A dermoscopy image of a single skin lesion.
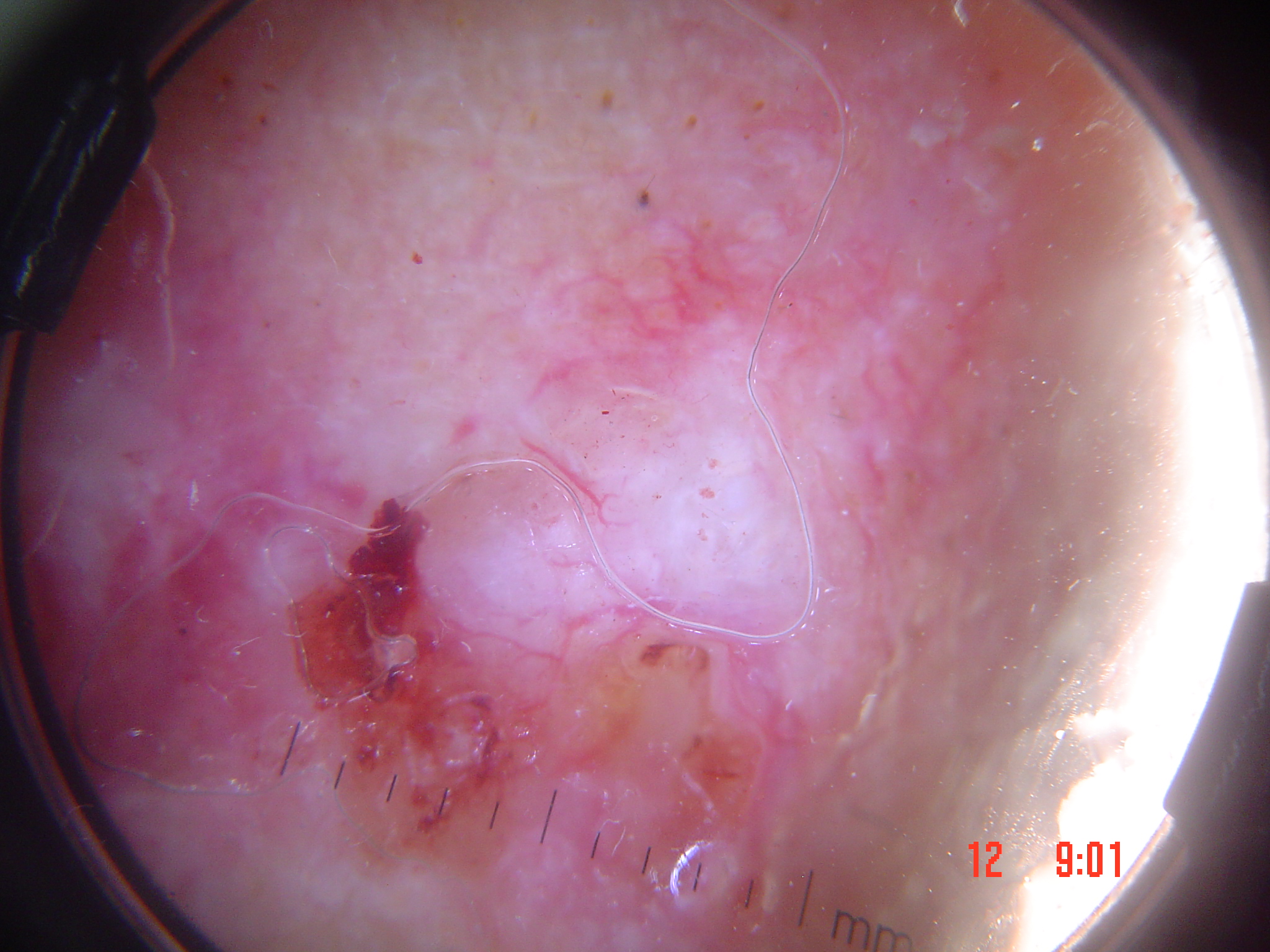Findings:
• pathology · basal cell carcinoma (biopsy-proven)